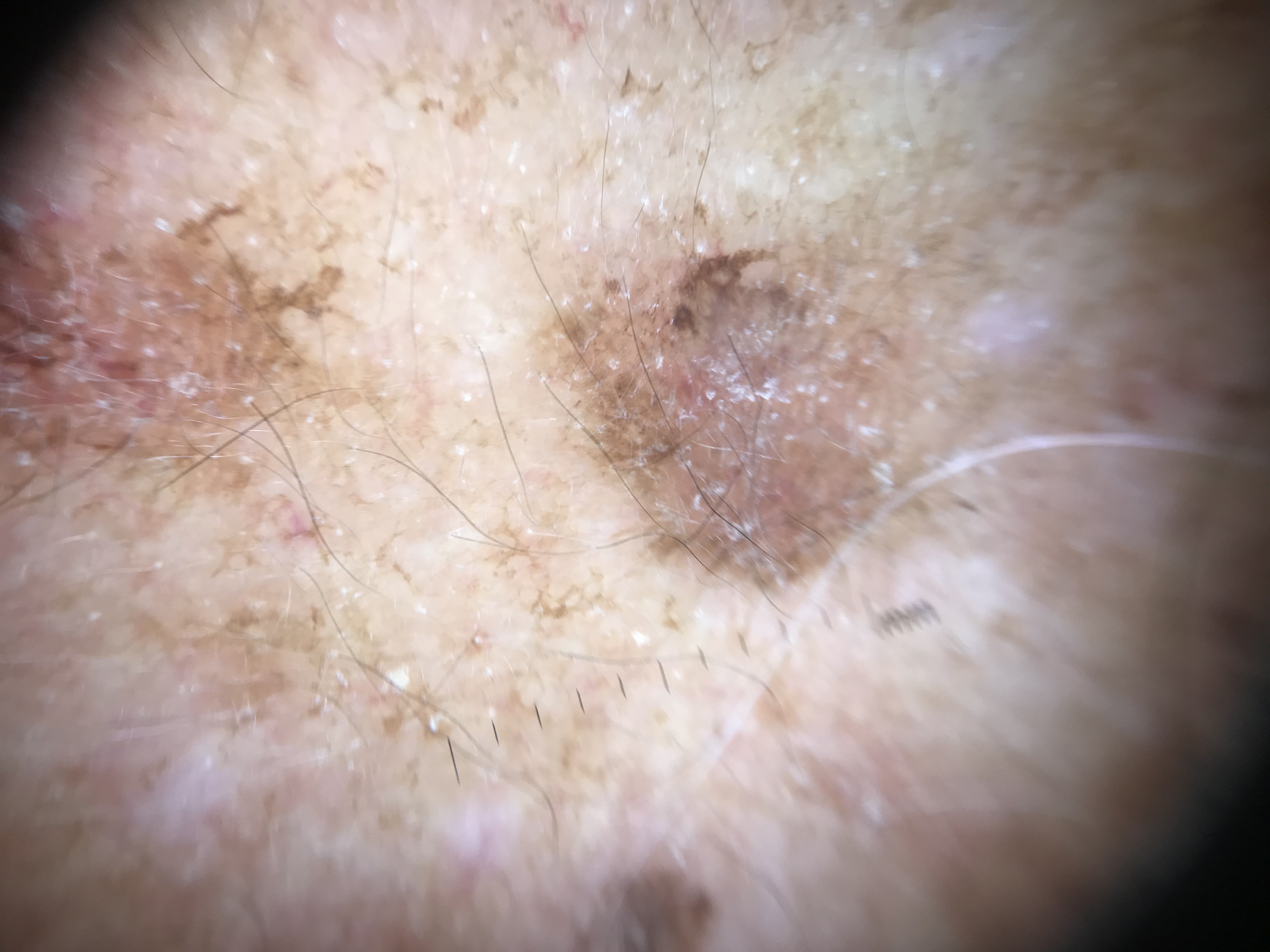label = actinic keratosis (expert consensus).